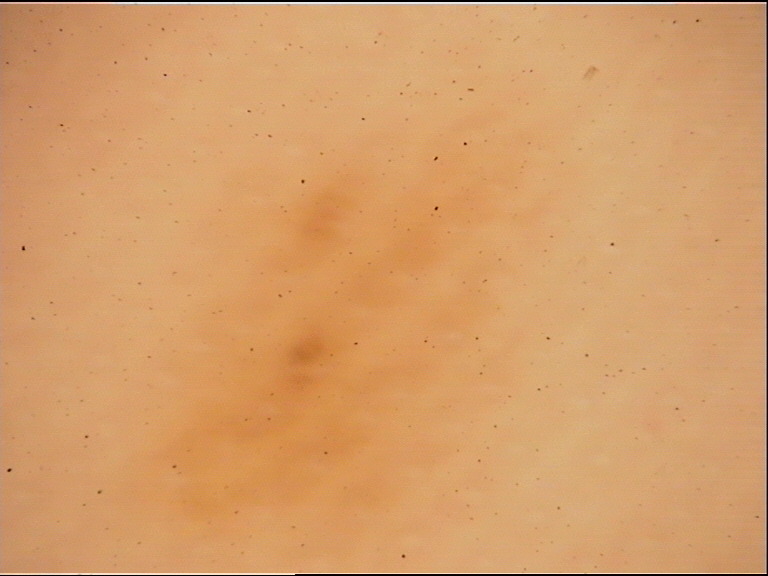label: acral junctional nevus (expert consensus).